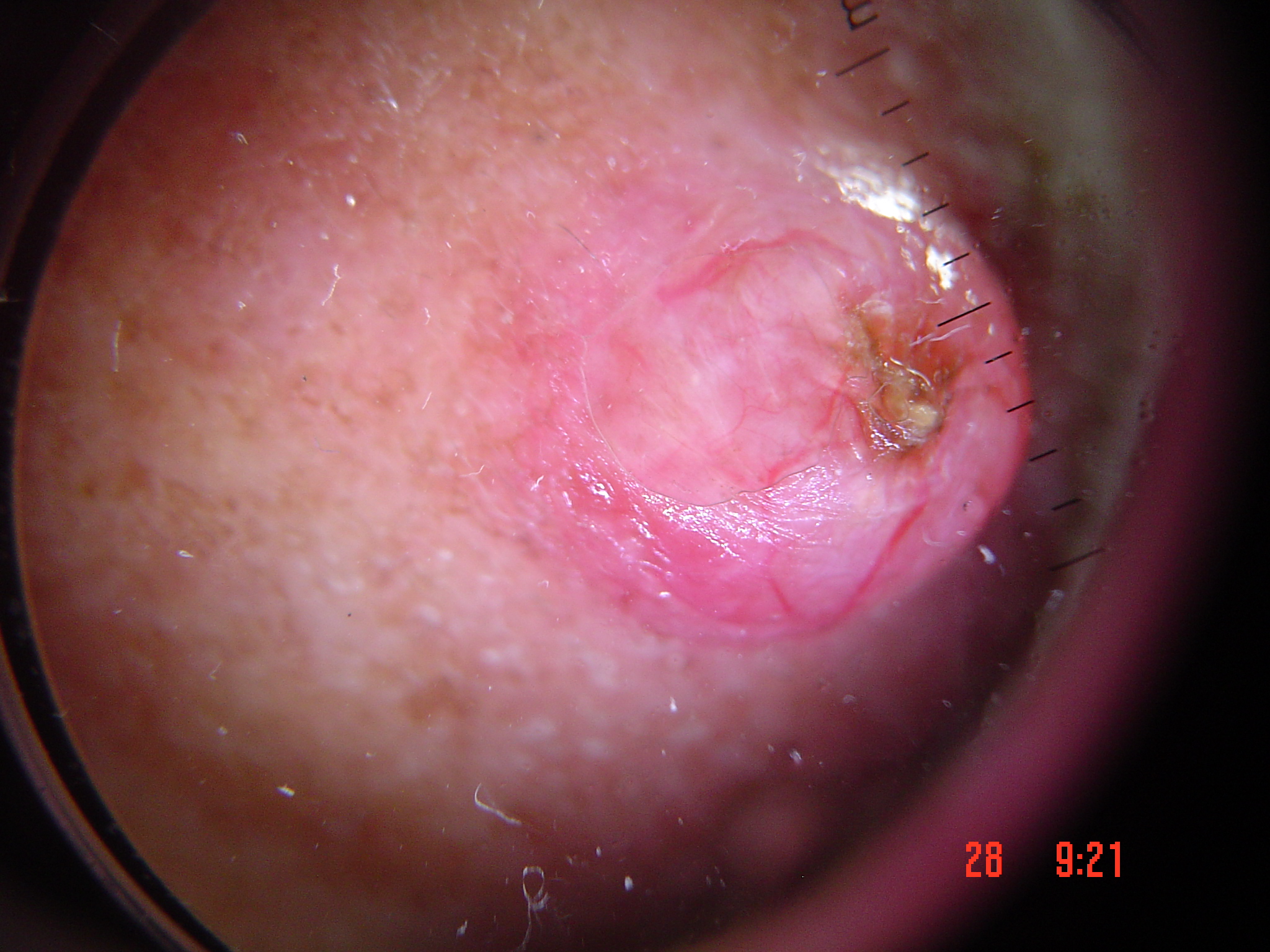A dermatoscopic image of a skin lesion. Histopathology confirmed a keratinocytic lesion — a basal cell carcinoma.